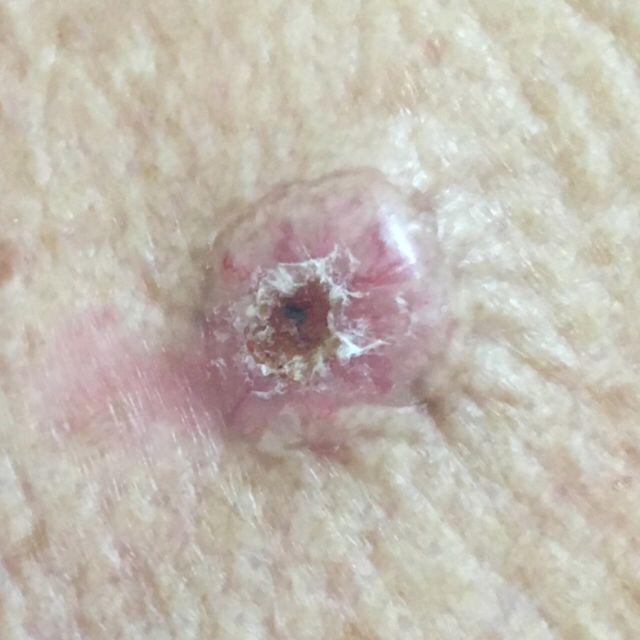– diagnostic label: basal cell carcinoma (biopsy-proven)